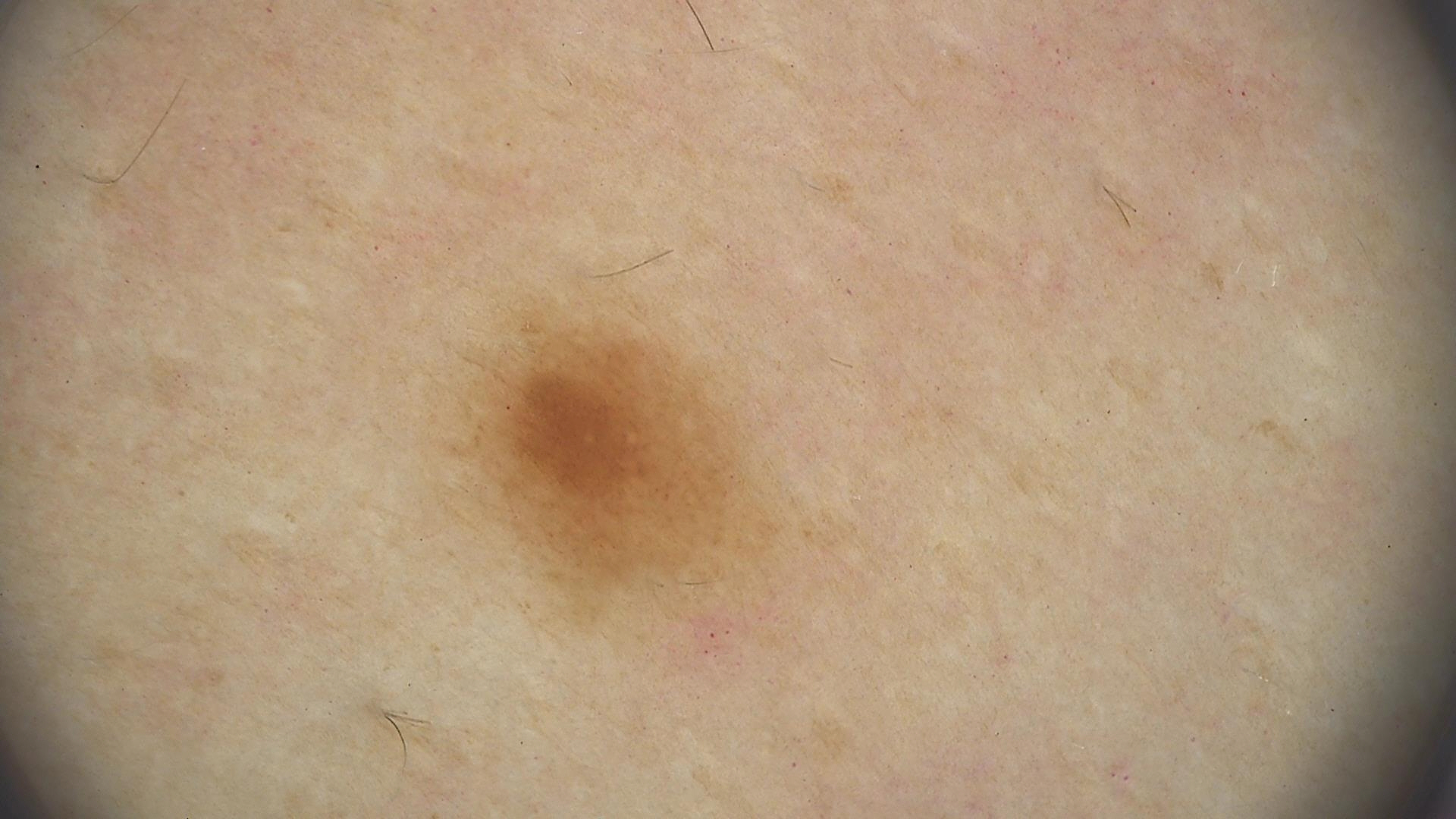image = dermatoscopy, classification = banal, class = junctional nevus (expert consensus).